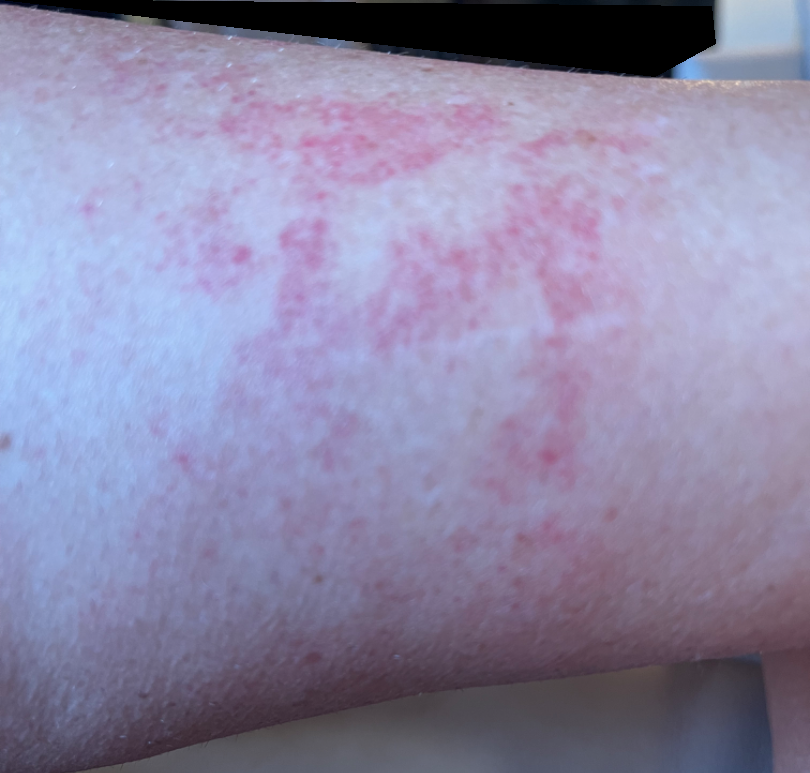{"differential": {"Pigmented purpuric eruption": 1.0}}